A dermoscopy image of a single skin lesion. A male subject in their mid- to late 60s:
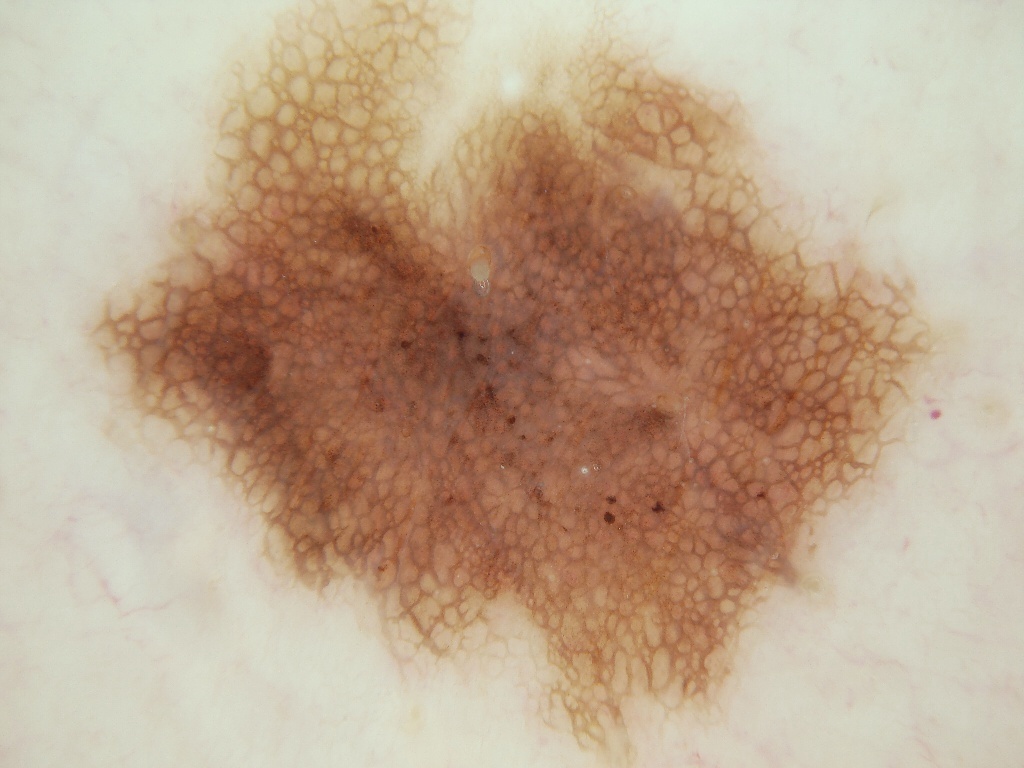lesion margin — reaches the image border | lesion location — bbox=[76, 0, 973, 763] | lesion size — ~53% of the field | dermoscopic pattern — pigment network and milia-like cysts | assessment — a melanocytic nevus.